No relevant systemic symptoms. Reported duration is less than one week. The contributor is a female aged 60–69. Self-categorized by the patient as a rash. Reported lesion symptoms include enlargement and itching. The photograph was taken at a distance. The arm is involved. The patient notes the lesion is raised or bumpy and fluid-filled: 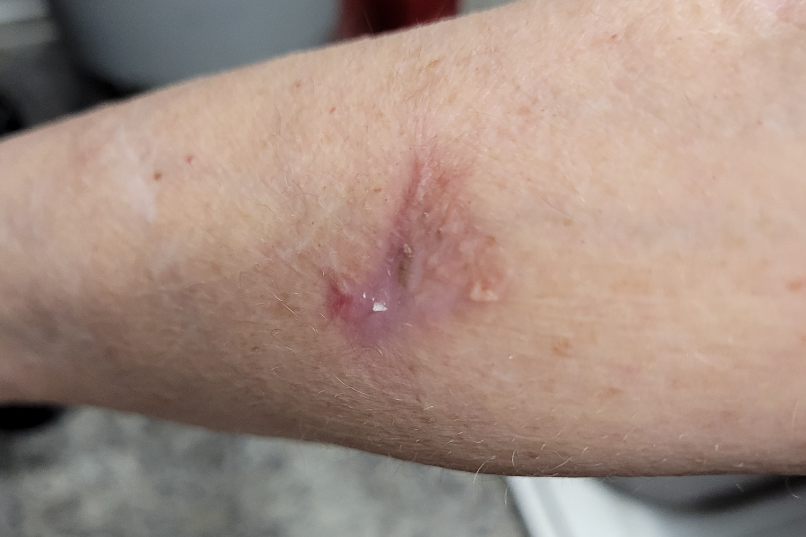Findings:
Scar Condition (primary).